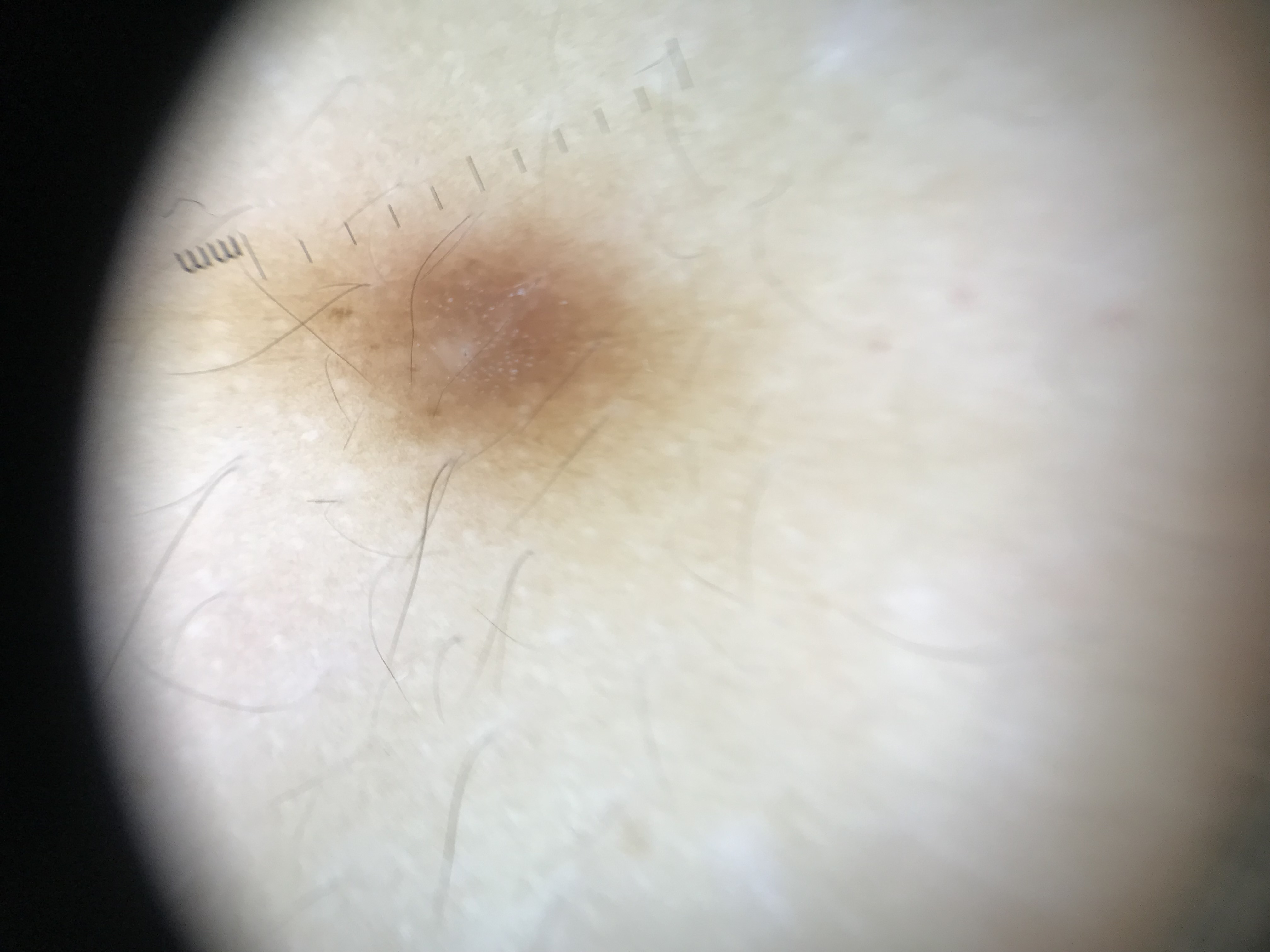Impression:
Labeled as a fibro-histiocytic, benign lesion — a dermatofibroma.